A dermatoscopic image of a skin lesion. A male subject 73 years old. Collected as part of a research study, without a referral diagnosis — 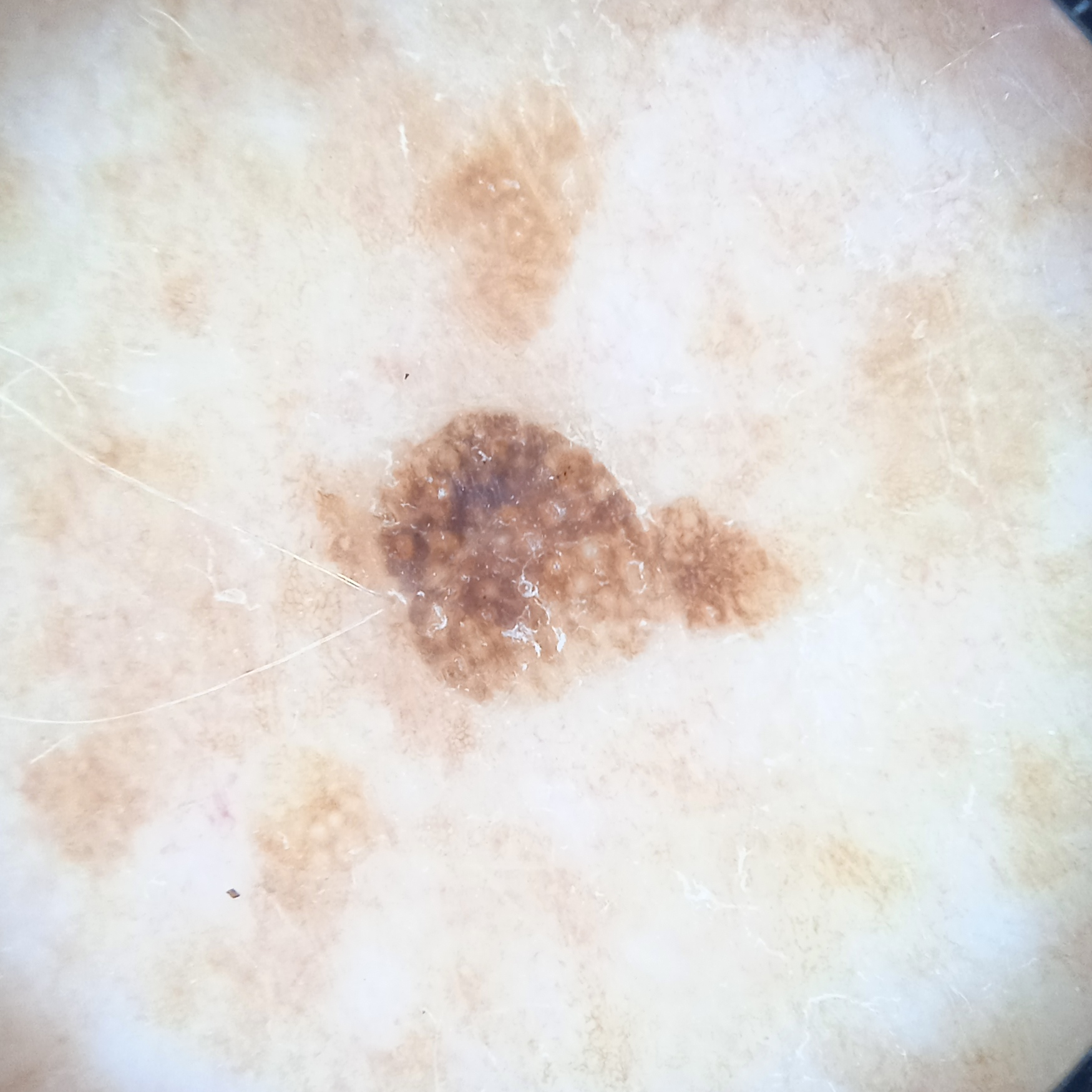The lesion is on the back.
The lesion measures approximately 5.5 mm.
The lesion was assessed as a seborrheic keratosis.